The lesion is associated with itching and enlargement · the contributor reports the condition has been present for one to four weeks · the contributor reports the lesion is raised or bumpy · the photo was captured at a distance · the leg is involved · the contributor reports associated fever, fatigue and joint pain — 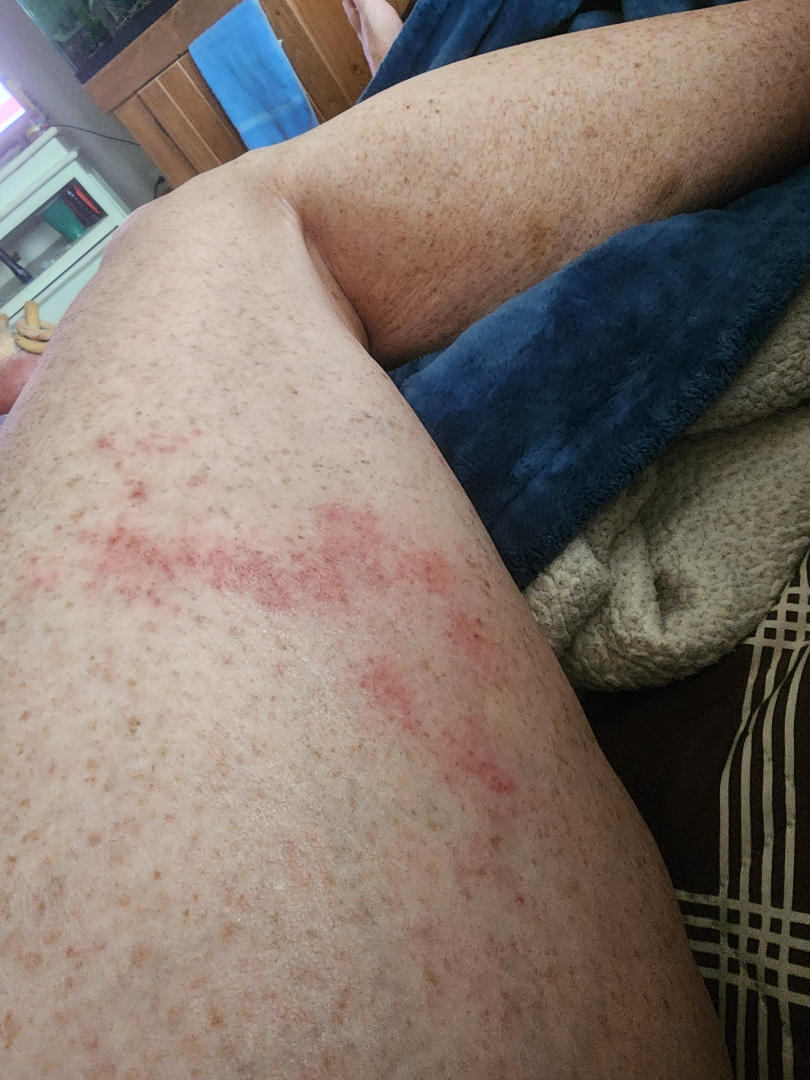Findings: The reviewing dermatologist was unable to assign a differential diagnosis from the image.